The patient is female, the lesion involves the arm, the photograph was taken at an angle.
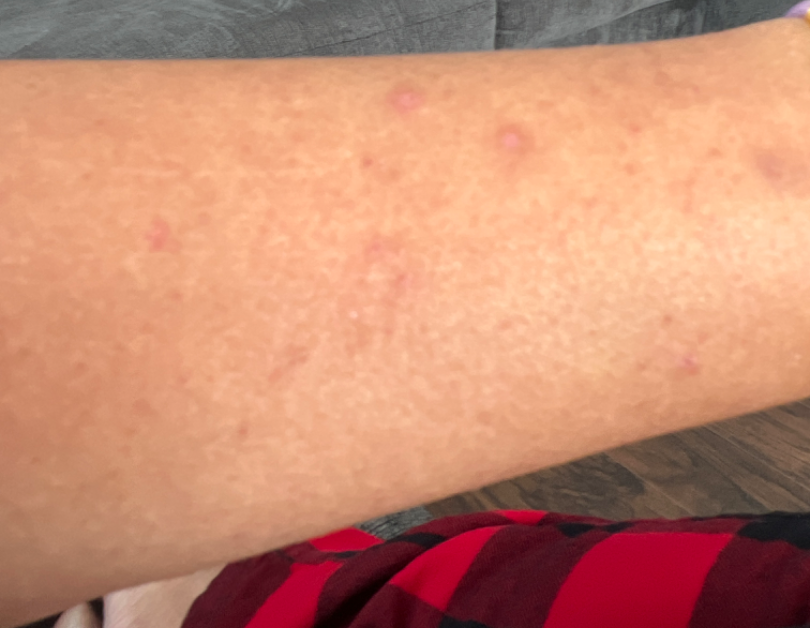Prurigo nodularis (weight 1.00).